The subject is male, the photo was captured at a distance, the affected area is the front of the torso.
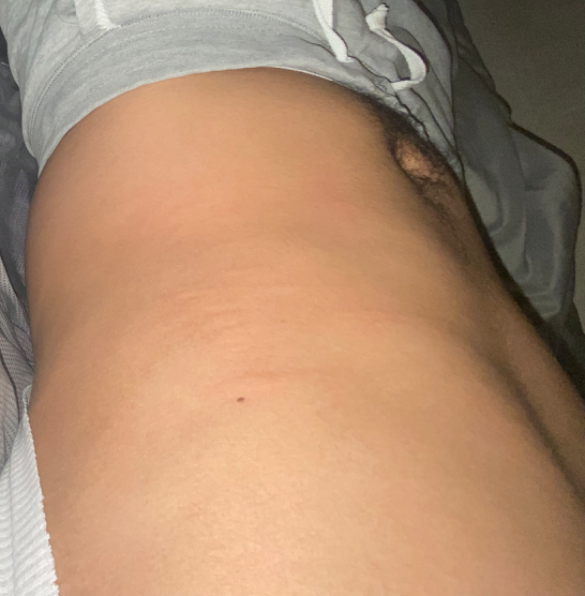{
  "differential": {
    "leading": [
      "Urticaria"
    ],
    "considered": [
      "Allergic Contact Dermatitis"
    ],
    "unlikely": [
      "Insect Bite"
    ]
  }
}